The photograph is a close-up of the affected area.
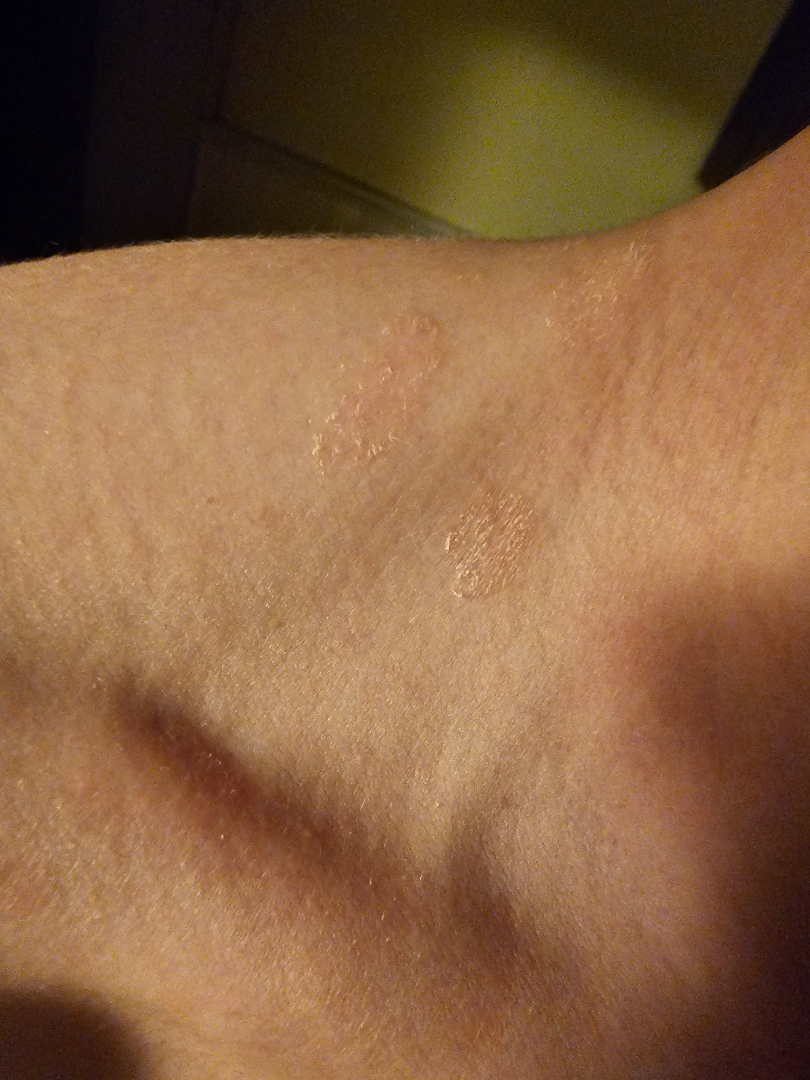Impression:
On remote review of the image: Pityriasis rosea (33%); Tinea Versicolor (33%); Seborrheic Dermatitis (33%).